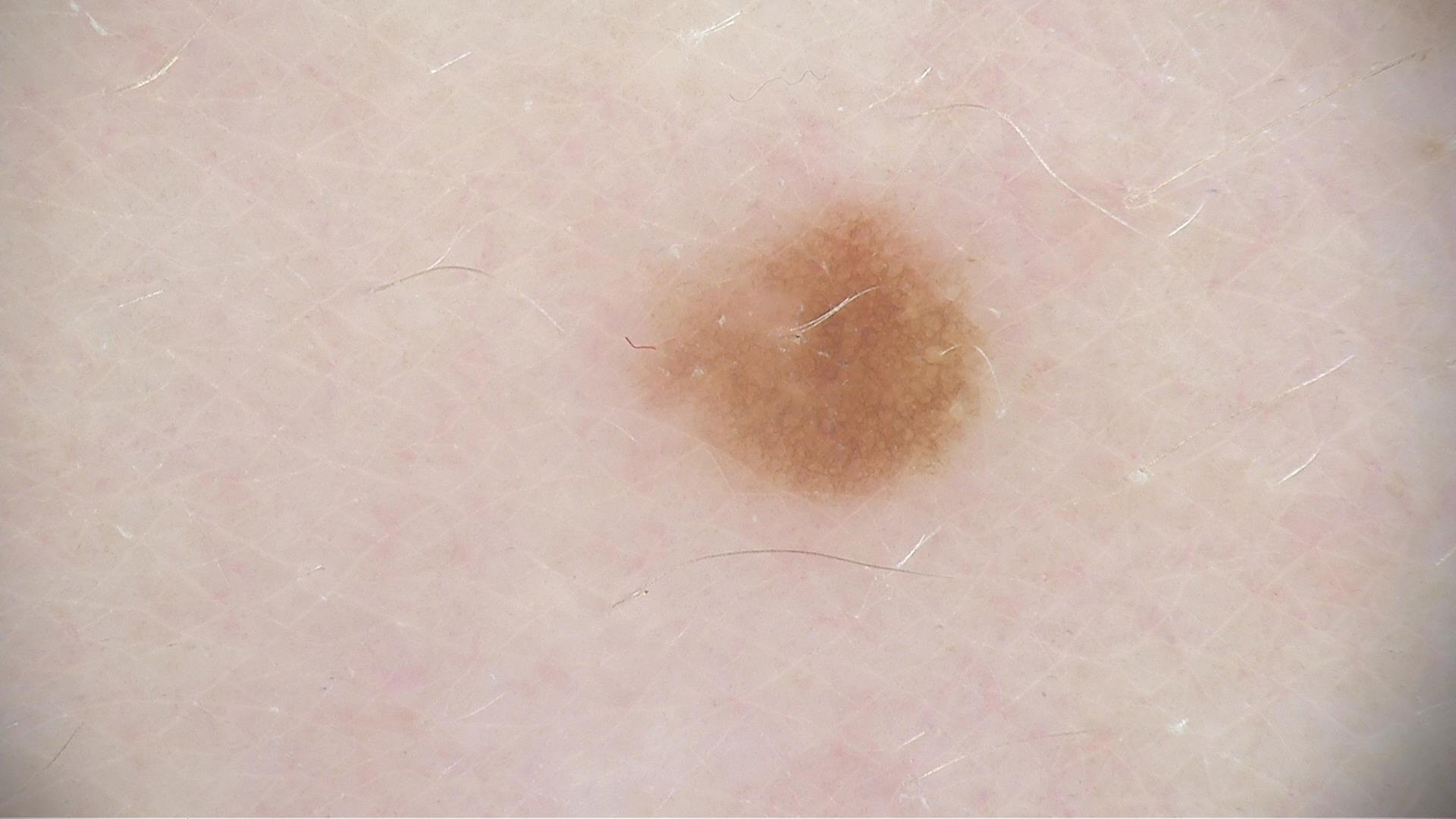diagnostic label: junctional nevus (expert consensus).